The lesion involves the leg. The subject is 30–39, female. An image taken at an angle — 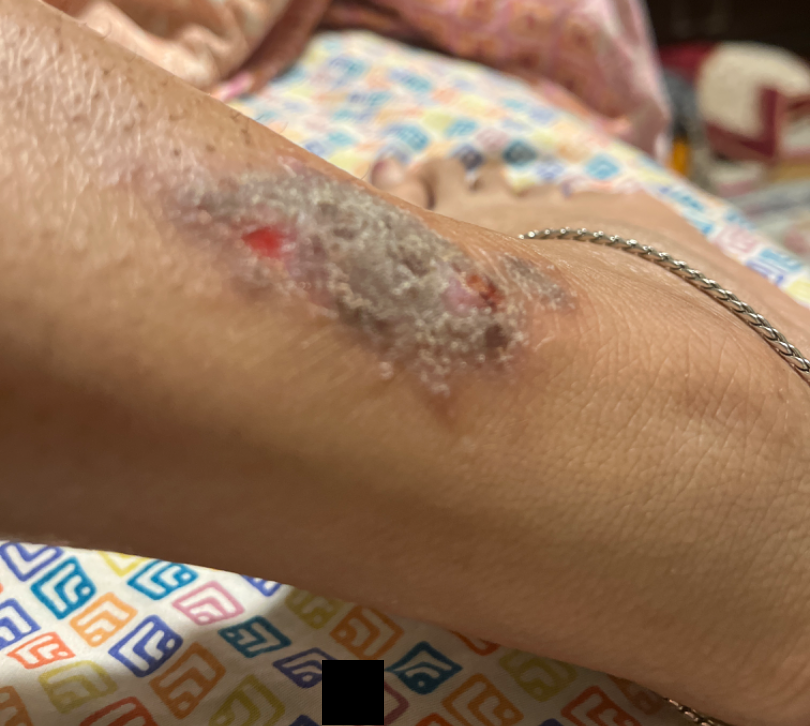On dermatologist assessment of the image, the leading impression is Lichen Simplex Chronicus; also on the differential is Mycetoma; less probable is Deep fungal infection; a more distant consideration is Lichen planus/lichenoid eruption.